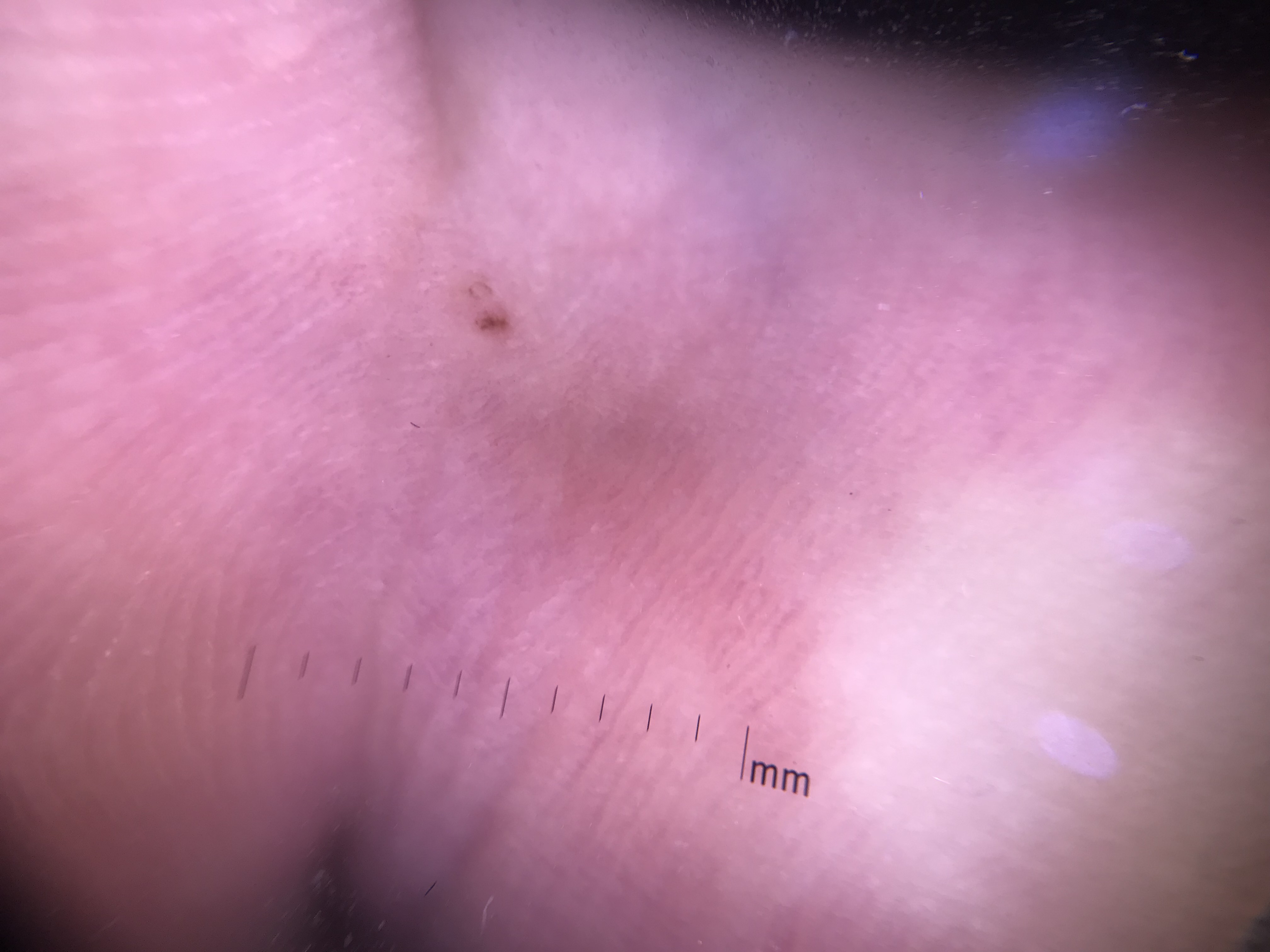Impression:
The diagnosis was an acral junctional nevus.